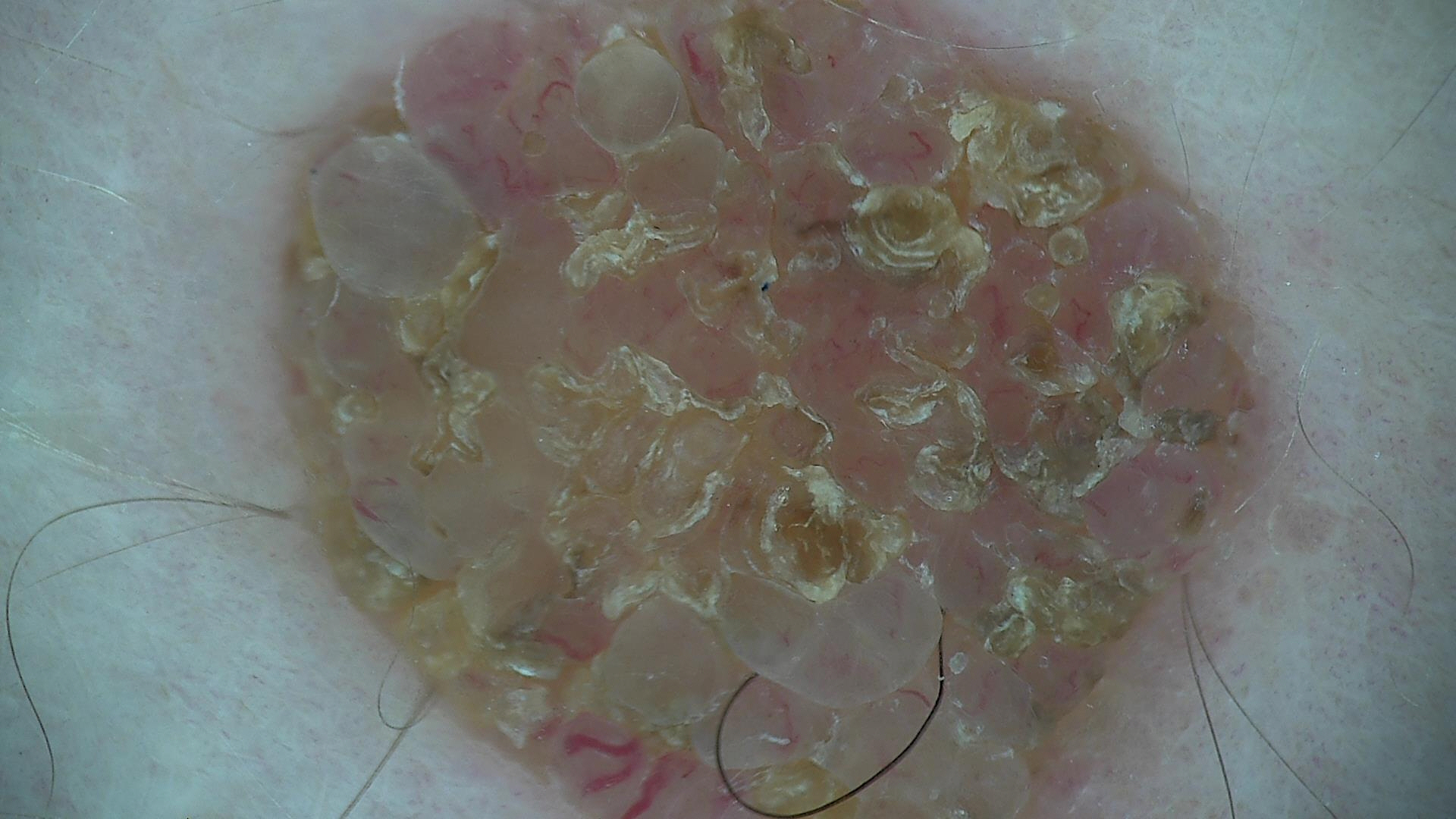A dermatoscopic image of a skin lesion.
The diagnosis was a banal lesion — a dermal nevus.